An image taken at a distance, located on the back of the hand — 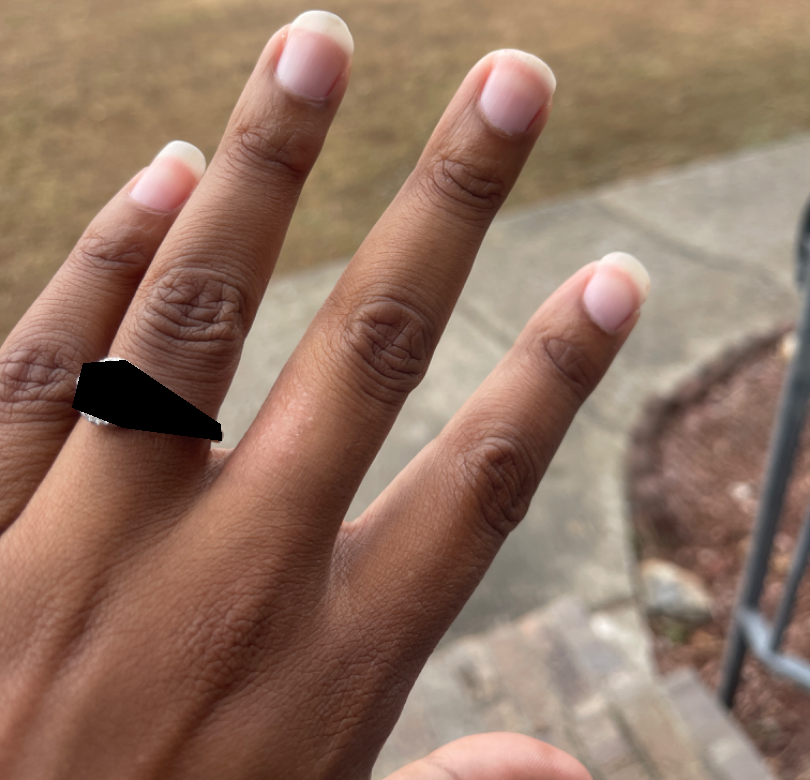Review:
The dermatologist could not determine a likely condition from the photograph alone.